A clinical photograph of a skin lesion · the patient reports a personal history of skin cancer · referred for assessment of suspected melanoma · a female subject 50 years of age.
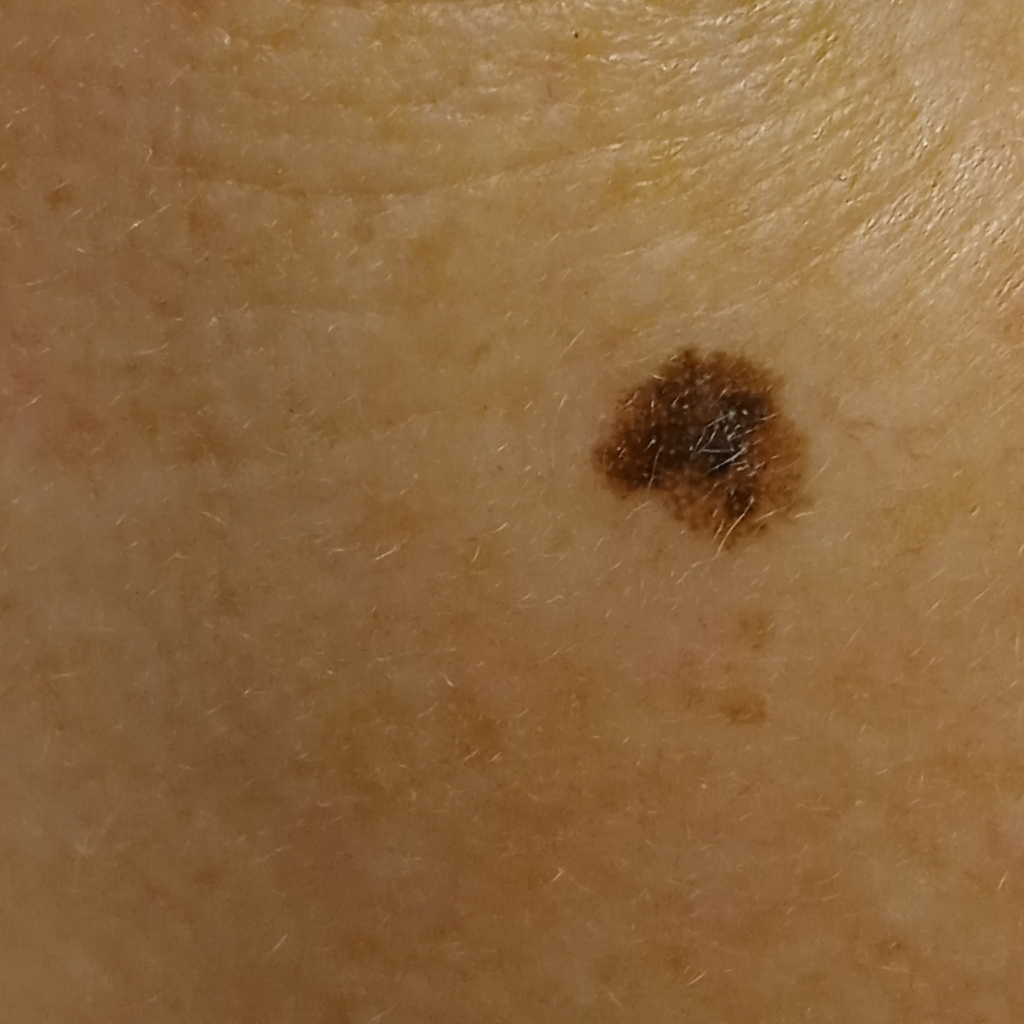body site: the face; lesion size: 7 mm; diagnostic label: melanoma (biopsy-proven).